This is a close-up image:
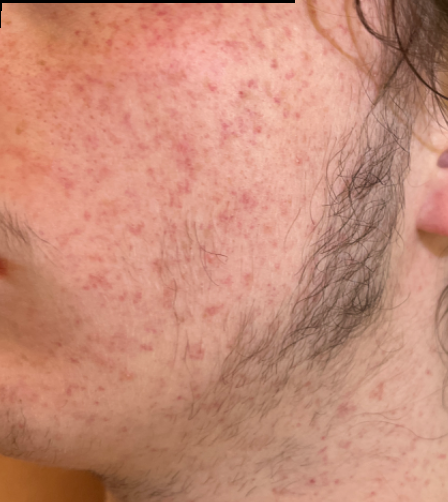* assessment: unable to determine
* skin tone: Fitzpatrick phototype II; non-clinician graders estimated 2 on the Monk skin tone scale